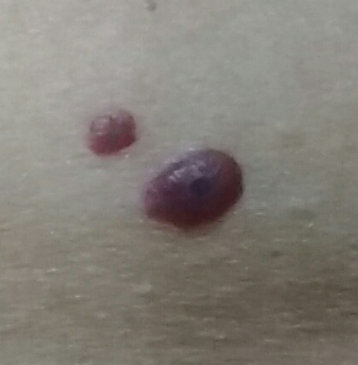<skin_lesion>
<patient>
<age>59</age>
</patient>
<image>clinical photo</image>
<lesion_location>the abdomen</lesion_location>
<symptoms>
<present>growth, elevation</present>
</symptoms>
<diagnosis>
<name>nevus</name>
<code>NEV</code>
<malignancy>benign</malignancy>
<confirmation>clinical consensus</confirmation>
</diagnosis>
</skin_lesion>